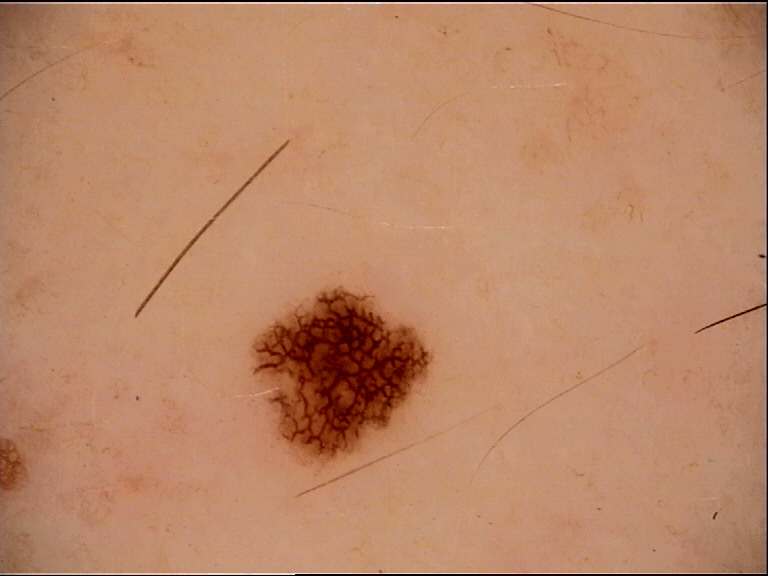diagnostic label=dysplastic junctional nevus (expert consensus).